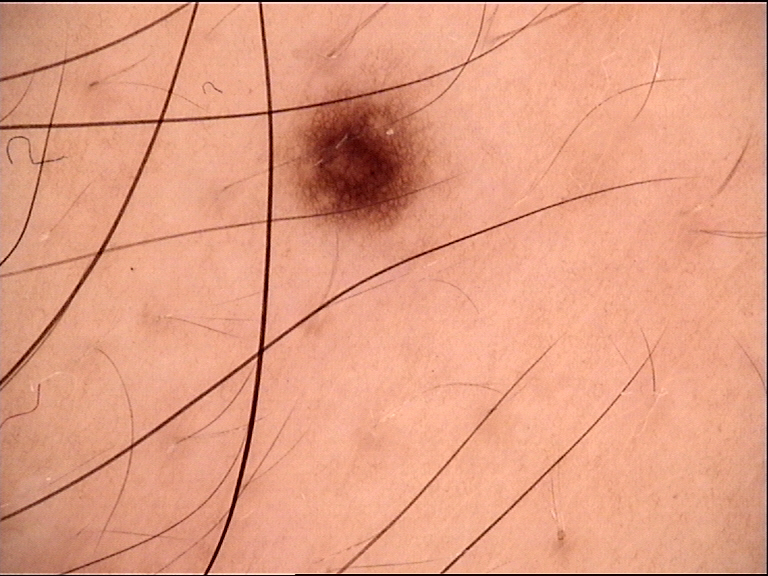Diagnosed as a junctional nevus.